The photograph is a close-up of the affected area.
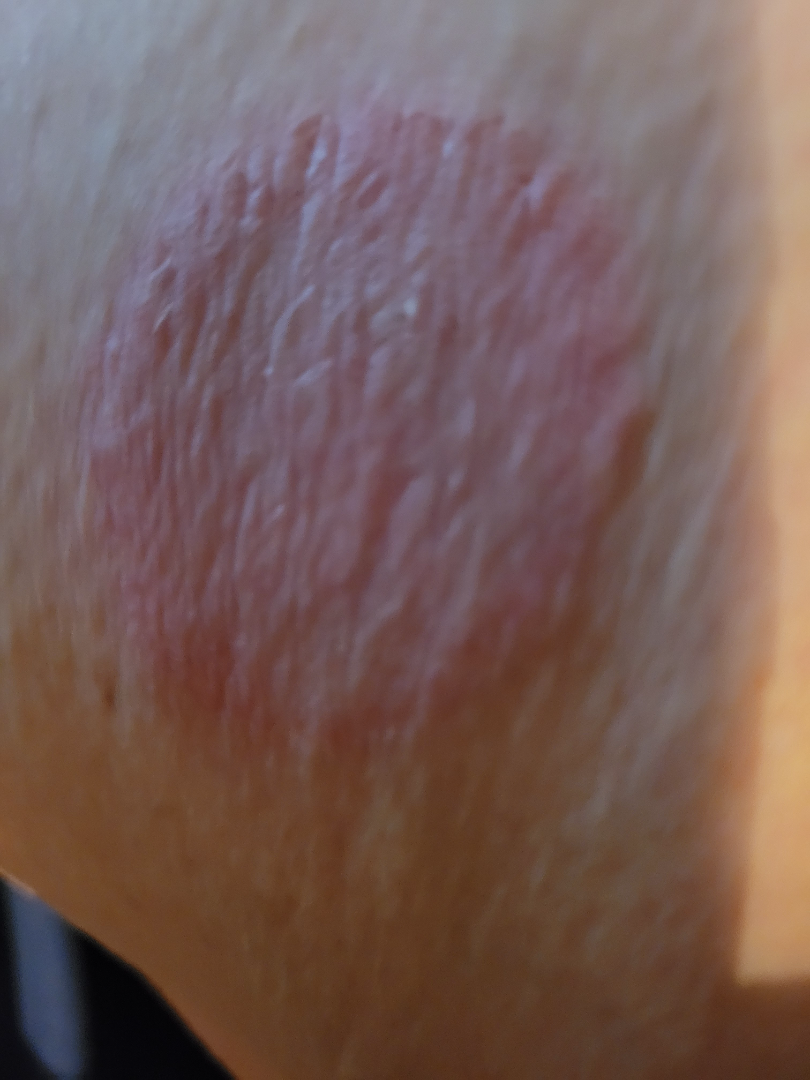Review: On photographic review, the leading impression is Tinea.